A female subject 27 years of age; a macroscopic clinical photograph of a skin lesion; collected as part of a research study, without a referral diagnosis: 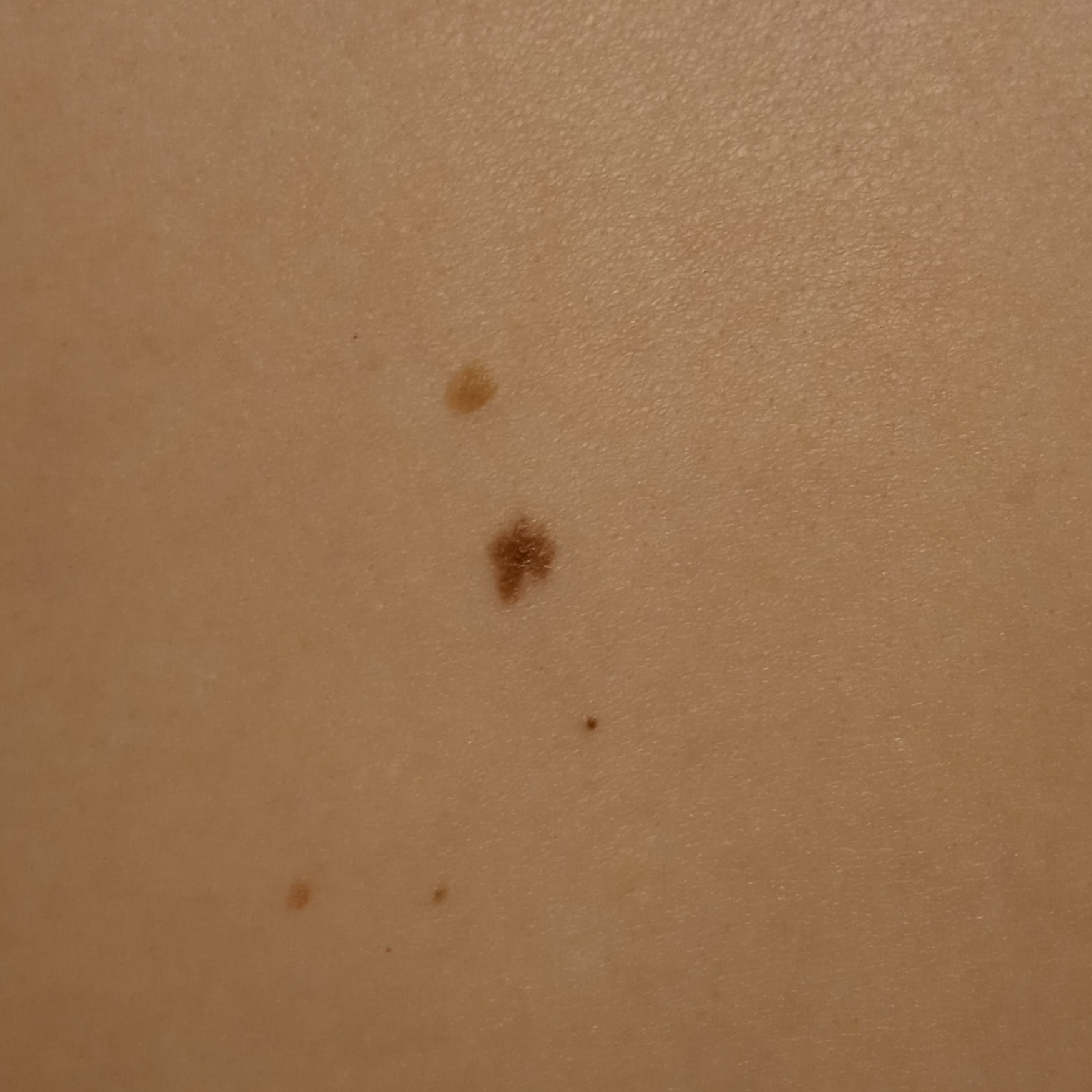The lesion is on the back.
Measuring roughly 5.9 mm.
Dermatologist review favored a melanocytic nevus.